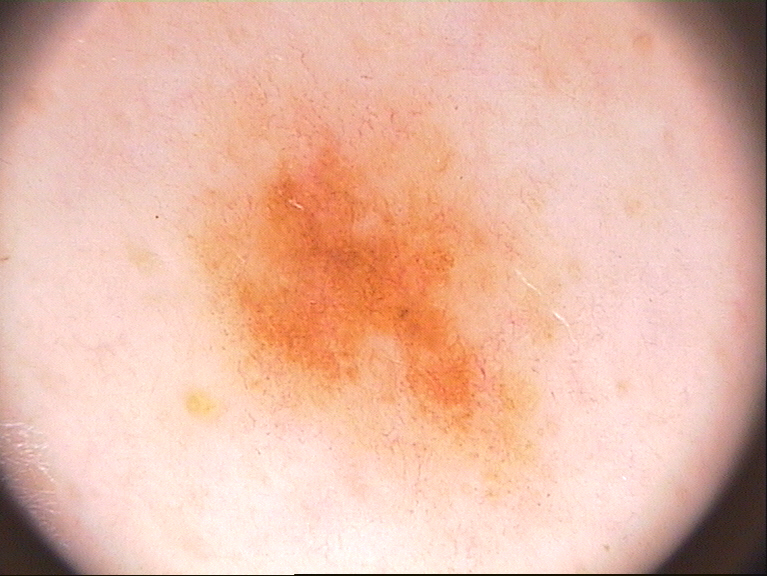This is a dermoscopic photograph of a skin lesion. A female patient aged 18 to 22. The lesion takes up about 40% of the image. On dermoscopy, the lesion shows pigment network. The lesion spans left=151, top=39, right=626, bottom=540. The diagnostic assessment was a melanocytic nevus, a benign lesion.